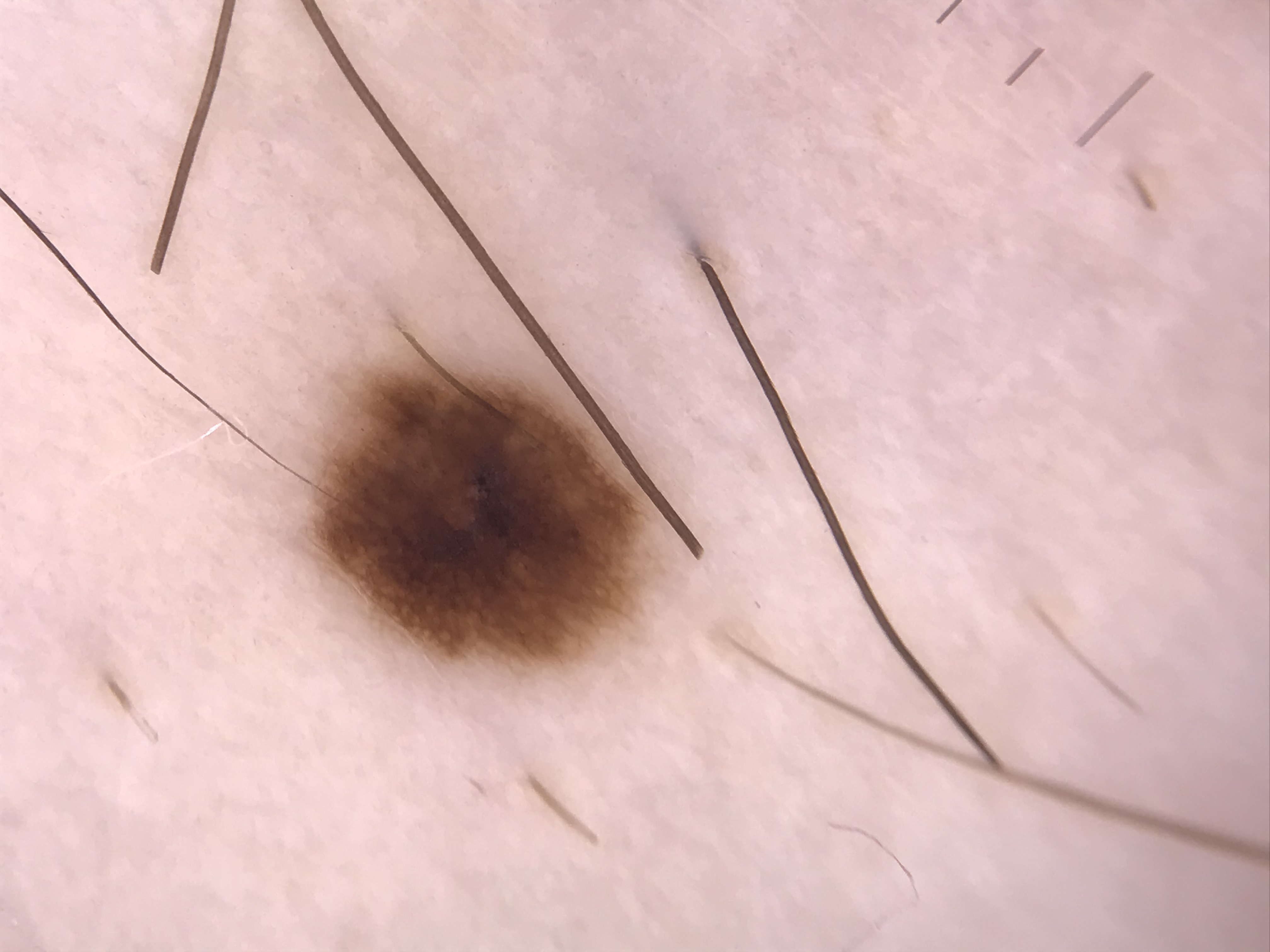The diagnostic label was a dysplastic junctional nevus.